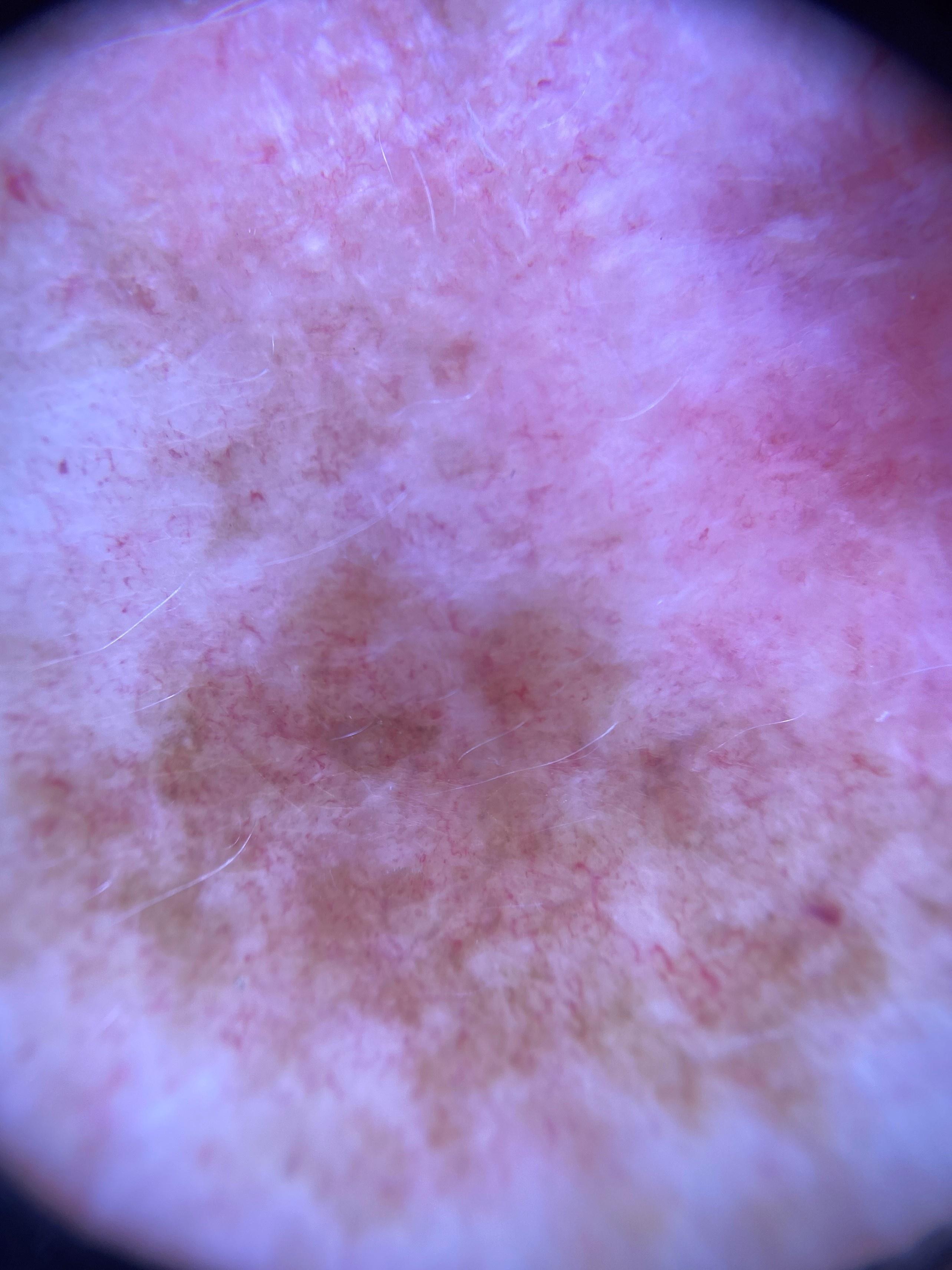image: contact-polarized dermoscopy | FST: II | subject: female, approximately 80 years of age | anatomic site: an upper extremity | diagnosis: Melanoma (biopsy-proven).